The contributor reports the condition has been present for about one day, the lesion involves the head or neck, the contributor reports the lesion is flat, an image taken at an angle, the contributor reports burning, the patient is a female aged 40–49 — 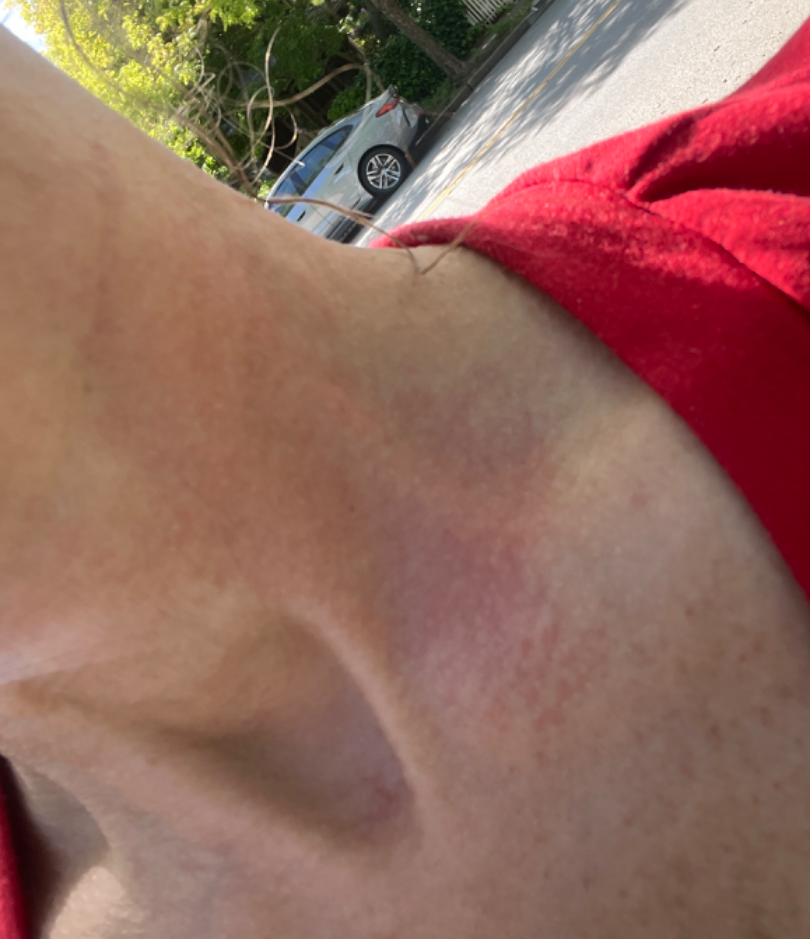Q: What is the differential diagnosis?
A: Allergic Contact Dermatitis (possible); Irritant Contact Dermatitis (possible)